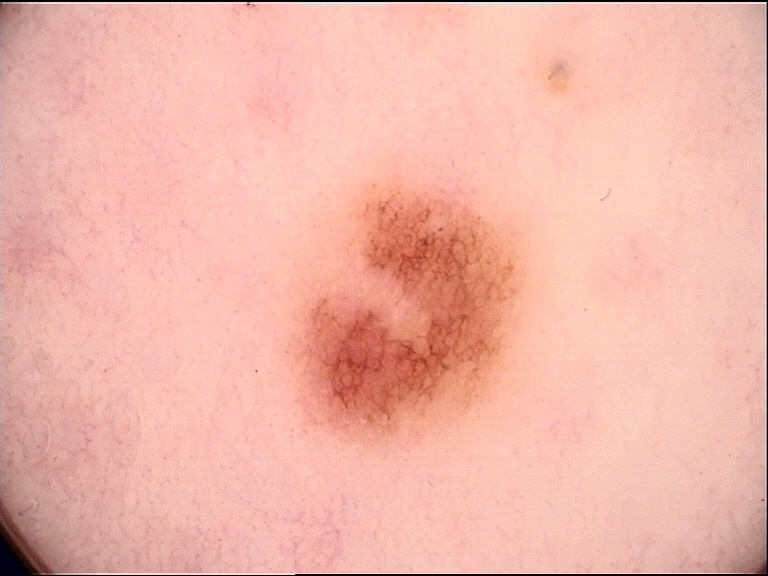Findings:
• diagnosis: dysplastic junctional nevus (expert consensus)